Recorded as skin type III. A female patient 46 years old. History notes prior malignancy (patient or family) and pesticide exposure: 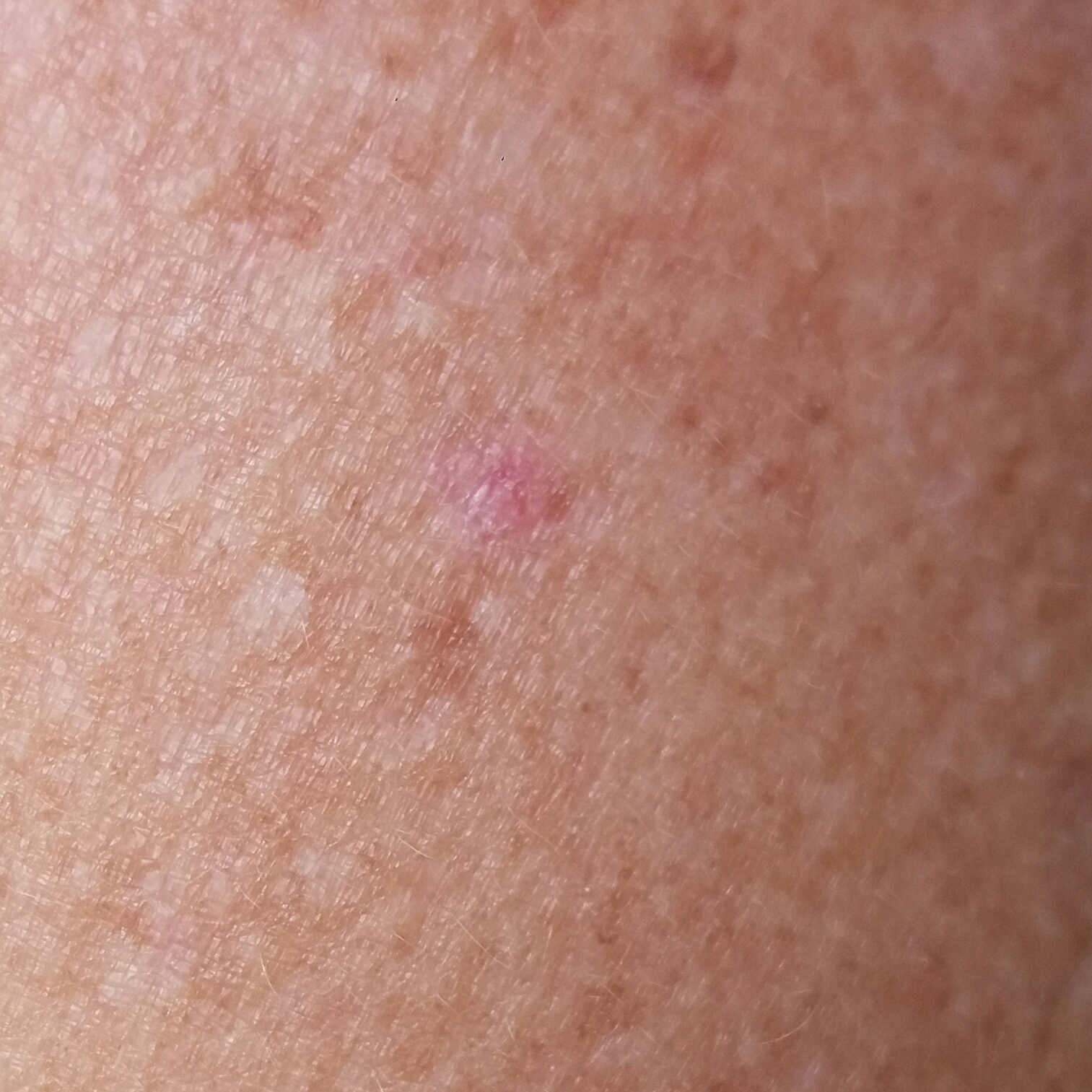Q: Where on the body is the lesion?
A: a hand
Q: How large is the lesion?
A: 4 × 3 mm
Q: What is the diagnosis?
A: actinic keratosis (clinical consensus)